A dermoscopic close-up of a skin lesion.
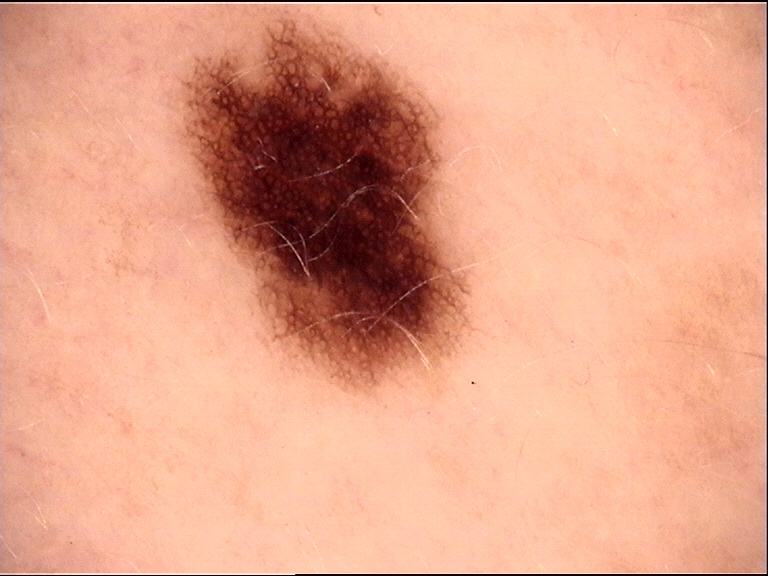Classified as a dysplastic junctional nevus.